The patient is 40–49, female · the photograph was taken at an angle: 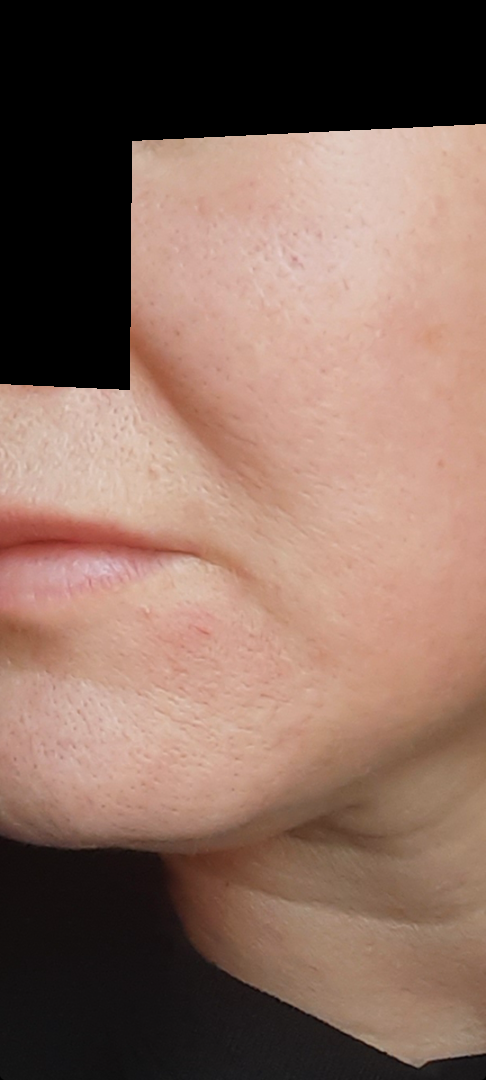| field | value |
|---|---|
| onset | more than five years |
| other reported symptoms | none reported |
| skin tone | Fitzpatrick skin type II |
| surface texture | raised or bumpy and rough or flaky |
| patient-reported symptoms | bothersome appearance |
| differential | most consistent with Perioral Dermatitis; with consideration of Irritant Contact Dermatitis; less probable is Perleche; less likely is Seborrheic Dermatitis; a remote consideration is Acne |